The lesion involves the back of the torso, arm, leg and front of the torso; present for about one day; Fitzpatrick skin type II; the contributor notes itching and bothersome appearance; the photograph was taken at an angle; texture is reported as raised or bumpy.
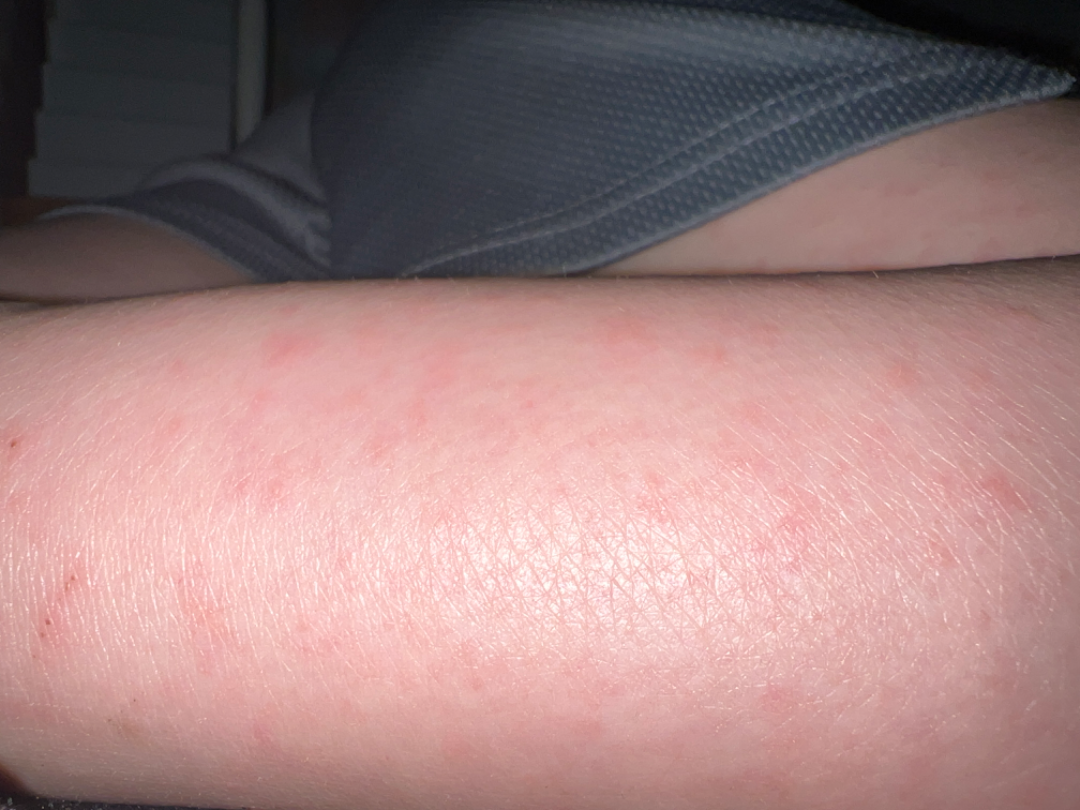clinical impression — favoring Viral Exanthem; with consideration of Drug Rash.